A skin lesion imaged with a dermatoscope.
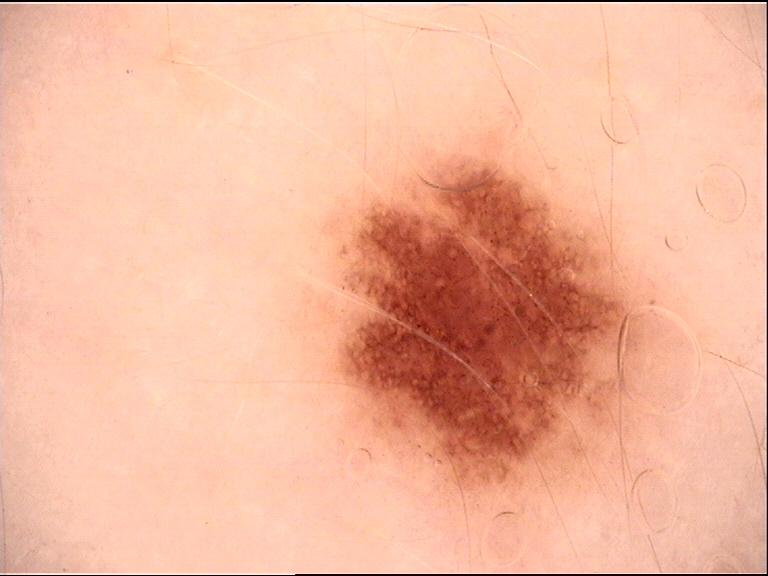This is a banal lesion. Labeled as a junctional nevus.